A dermoscopic view of a skin lesion — 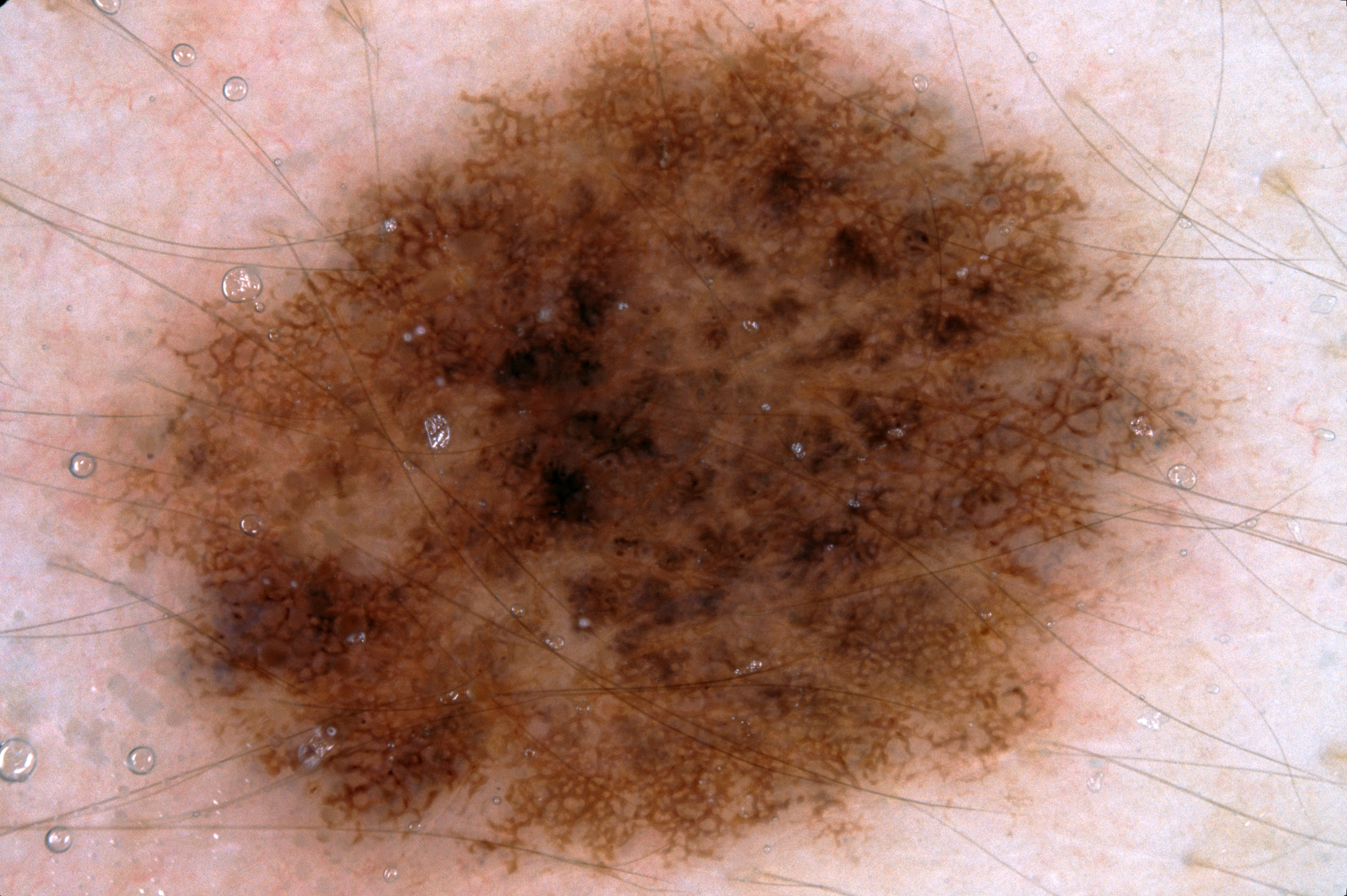• dermoscopic pattern · pigment network; absent: negative network, streaks, and milia-like cysts
• lesion bbox · <bbox>60, 17, 1197, 887</bbox>
• lesion size · ~54% of the field
• impression · a melanocytic nevus